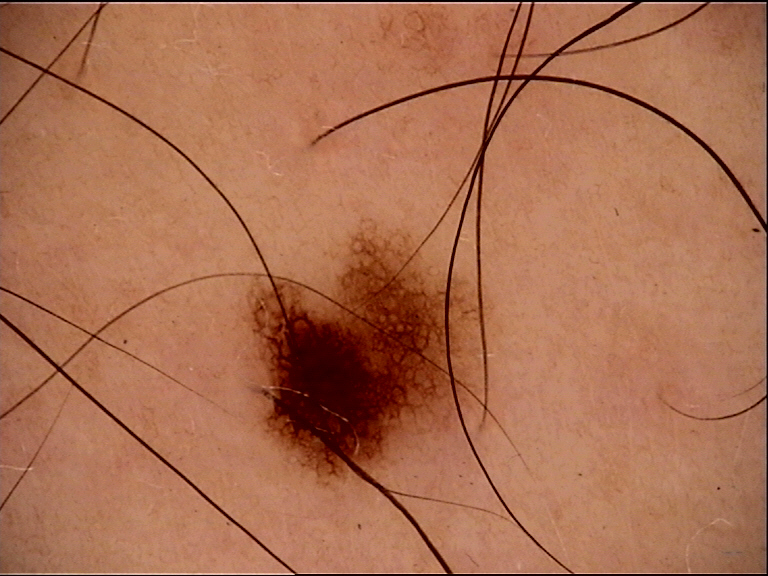Findings:
– assessment — dysplastic junctional nevus (expert consensus)